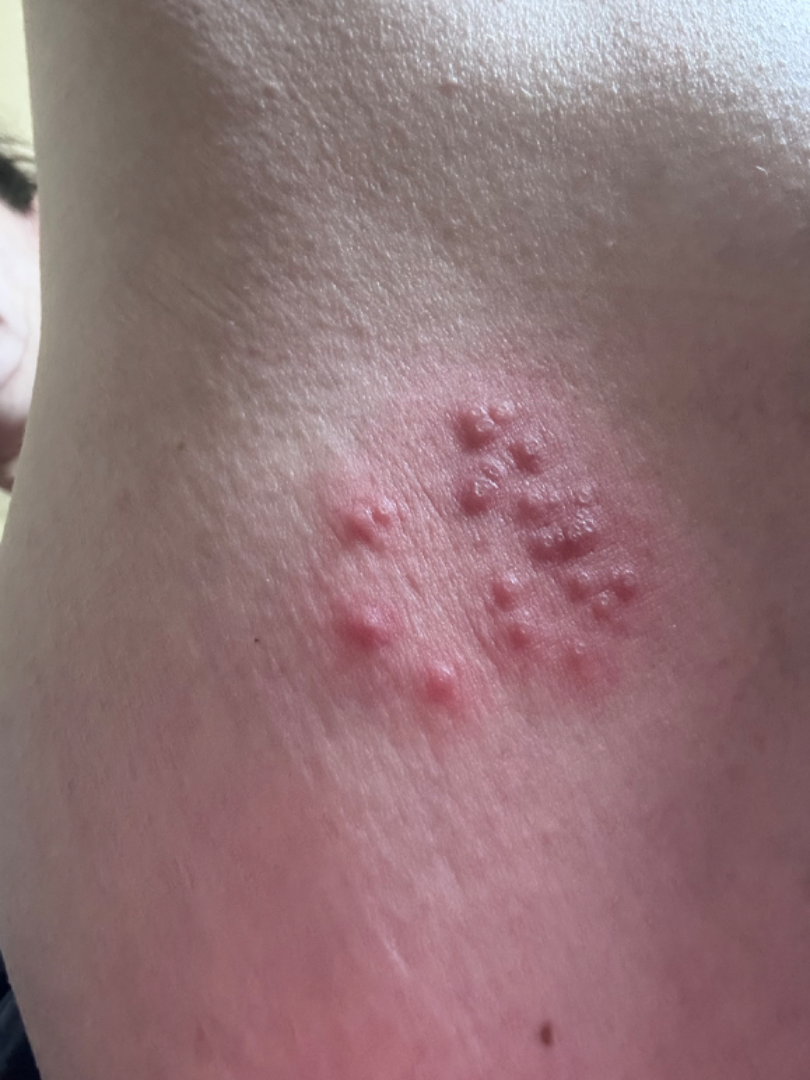This image was taken at a distance.
The subject is 50–59, female.
The lesion is described as raised or bumpy.
Located on the leg.
The lesion is associated with pain, enlargement and burning.
Present for less than one week.
Most consistent with Molluscum Contagiosum; the differential also includes Impetigo; with consideration of Herpes Simplex.